A dermoscopic photograph of a skin lesion.
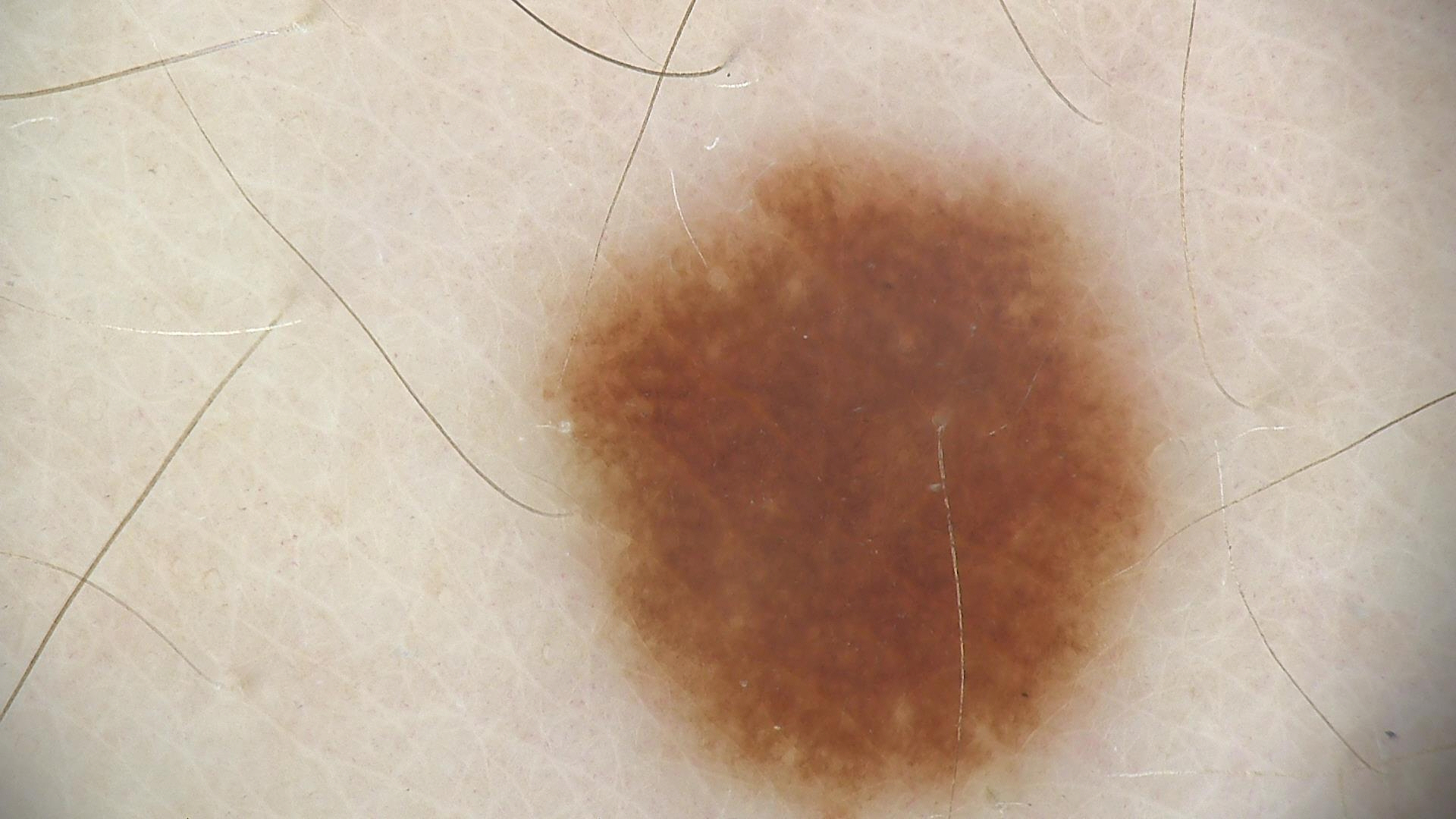Impression:
Labeled as a dysplastic junctional nevus.